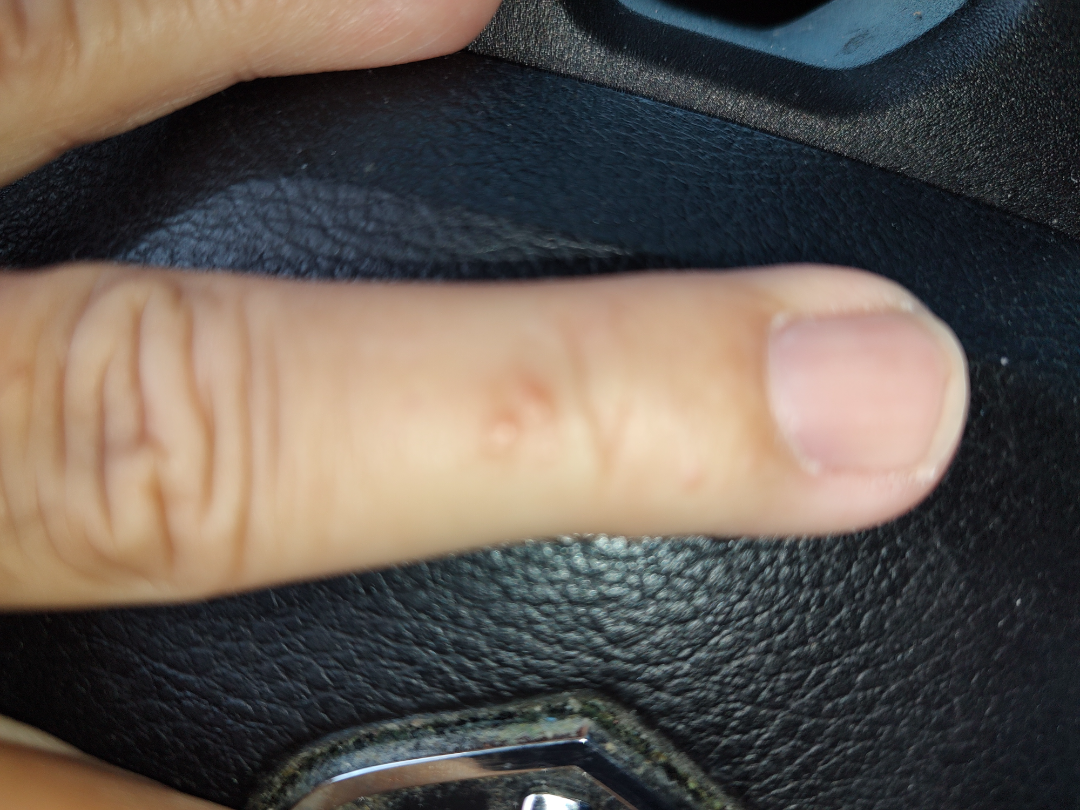Notes:
* assessment: indeterminate